A dermoscopic image of a skin lesion.
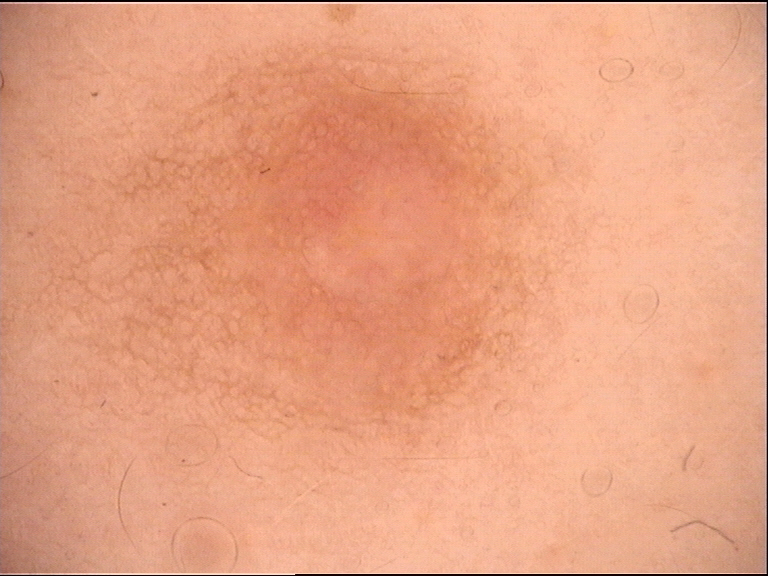  lesion_type:
    main_class: banal
    pattern: dermal
  diagnosis:
    name: dermal nevus
    code: db
    malignancy: benign
    super_class: melanocytic
    confirmation: expert consensus